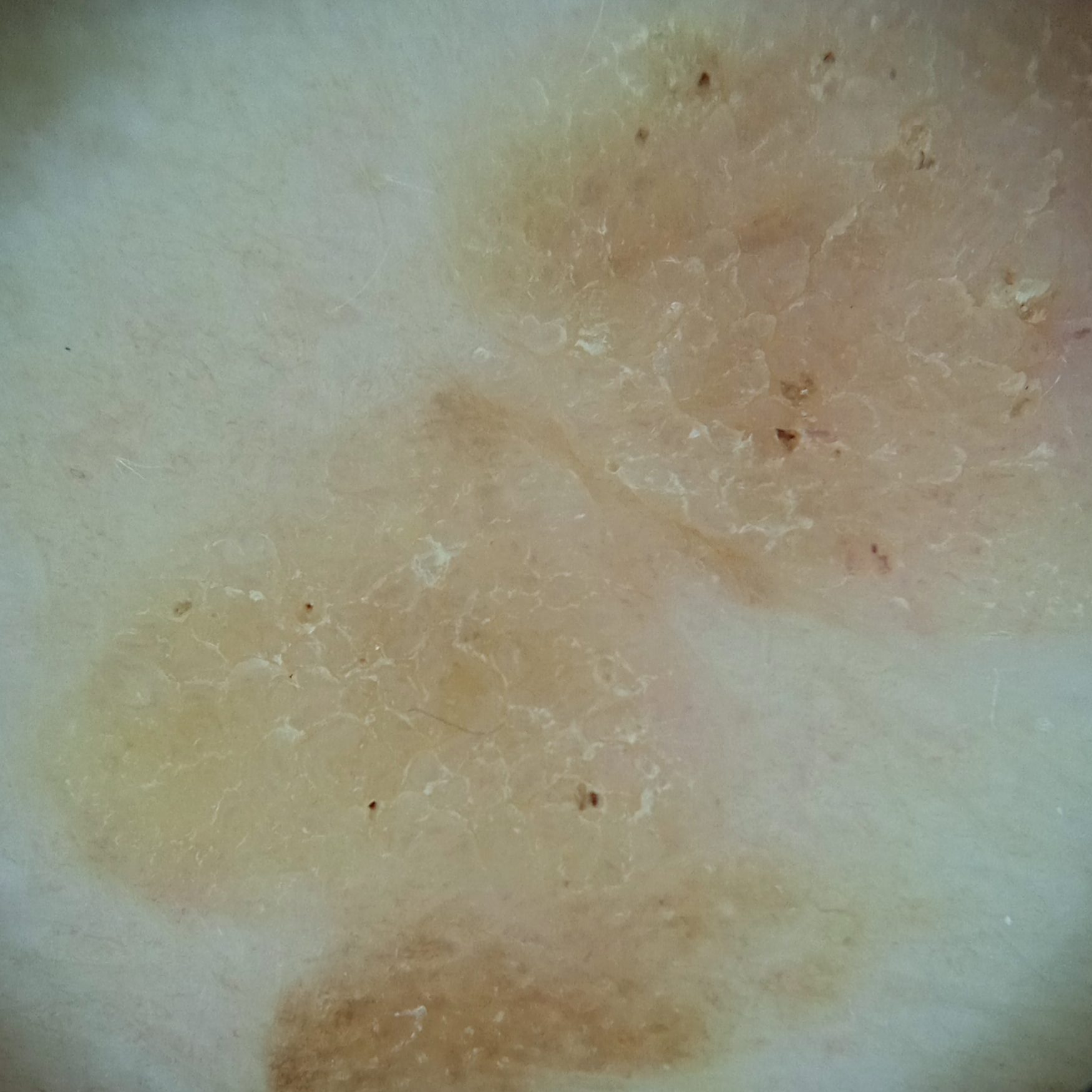Findings:
• modality — dermatoscopic image
• sun reaction — skin reddens painfully with sun exposure
• nevus count — a moderate number of melanocytic nevi
• clinical context — research study (no referral diagnosis)
• patient — female, aged 81
• location — the back
• assessment — seborrheic keratosis (dermatologist consensus)